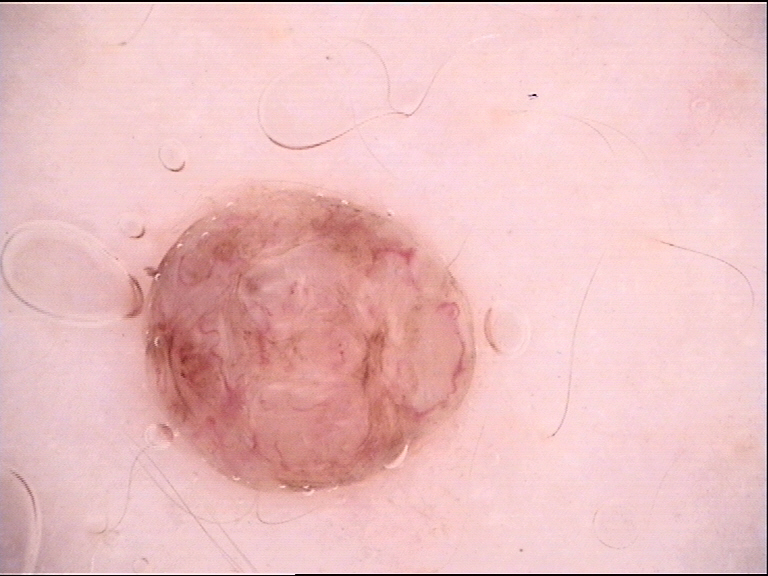A dermoscopic image of a skin lesion.
This is a banal lesion.
The diagnostic label was a dermal nevus.